A male subject aged 78-82; the patient is FST II; a clinical photograph showing a skin lesion in context; the chart records a prior melanoma:
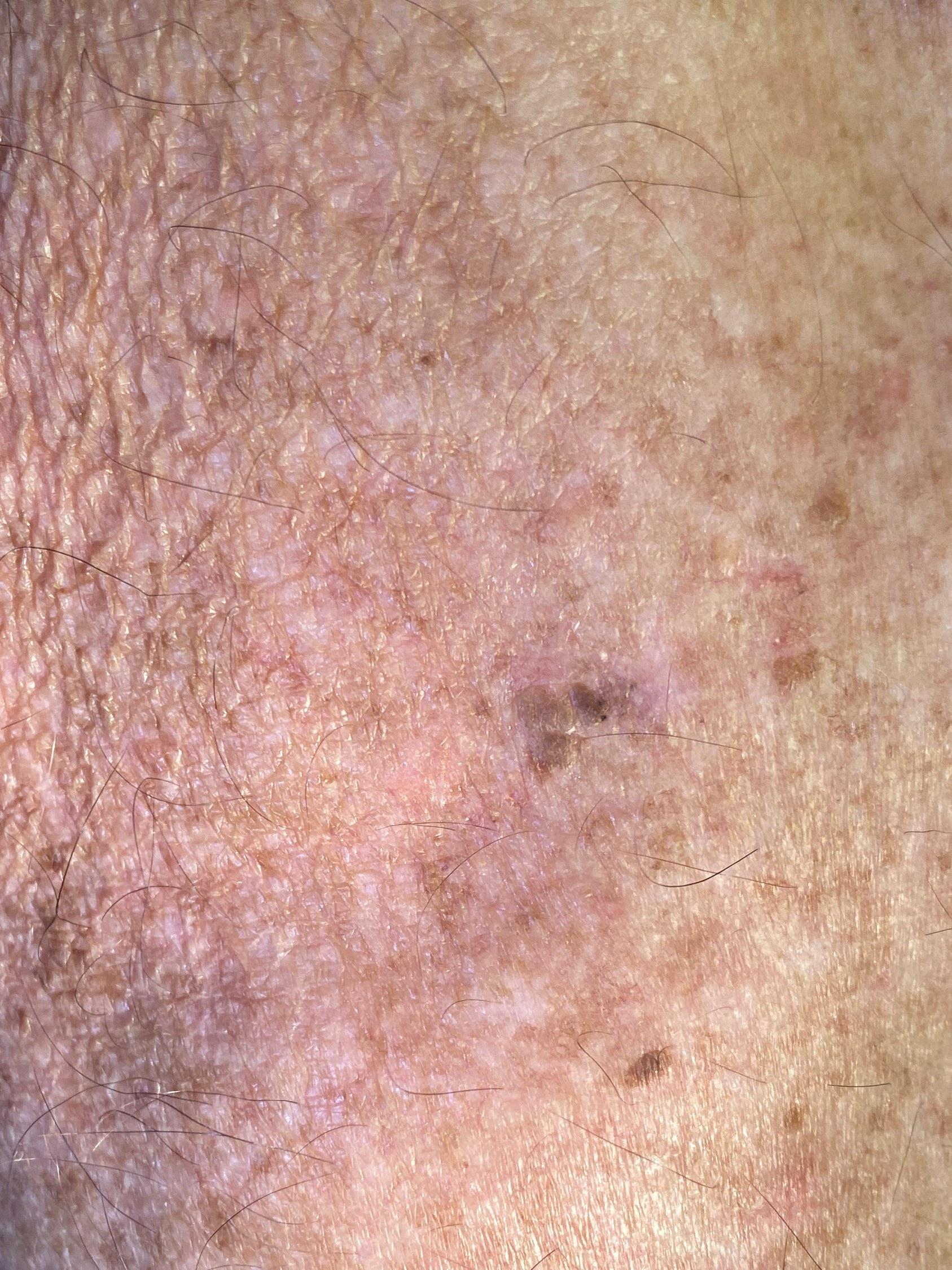Q: Where on the body is the lesion?
A: an upper extremity
Q: What did the workup show?
A: Seborrheic keratosis (biopsy-proven)